A male subject aged 33 to 37 · a dermoscopic view of a skin lesion: 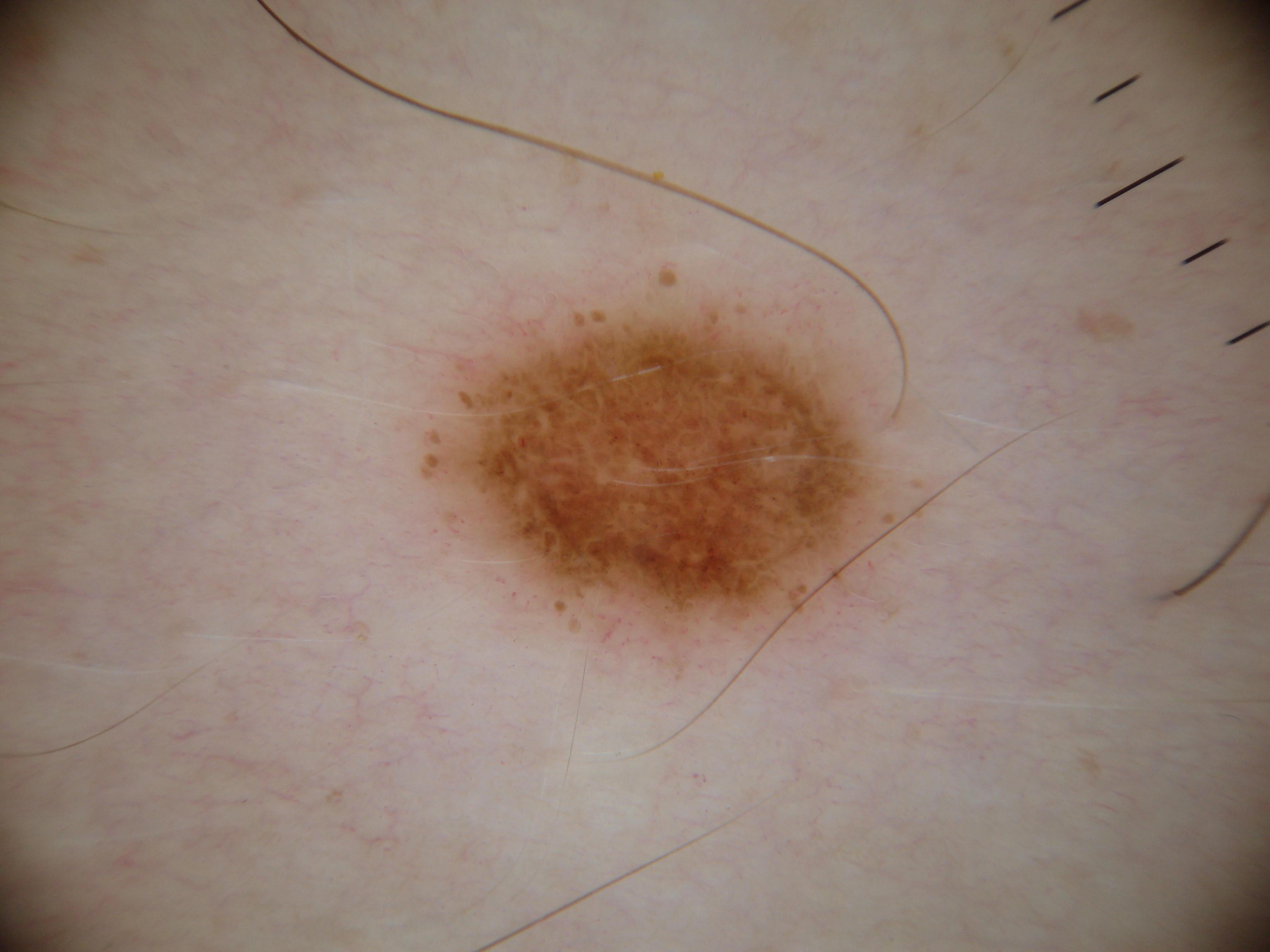The dermoscopic pattern shows globules and negative network. As (left, top, right, bottom), lesion location: [398,246,946,691]. Biopsy-confirmed as a melanoma, a malignant skin lesion.